Acquired for a research image collection, with no referral diagnosis. A female subject 75 years of age. A dermoscopy image of a skin lesion: 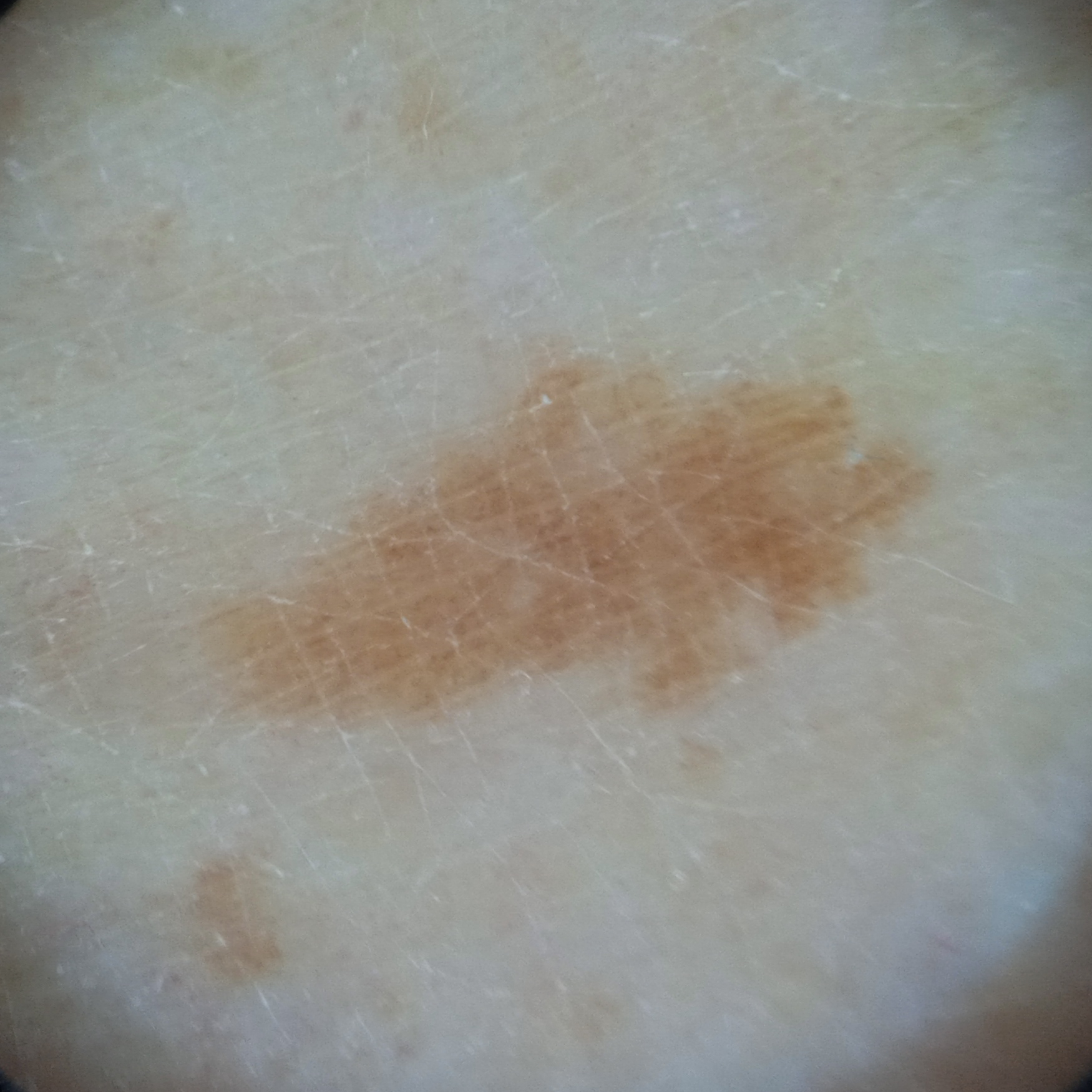Findings:
- anatomic site: a leg
- size: 8.2 mm
- diagnosis: melanocytic nevus (dermatologist consensus)